This is a dermoscopic photograph of a skin lesion; a female patient about 35 years old.
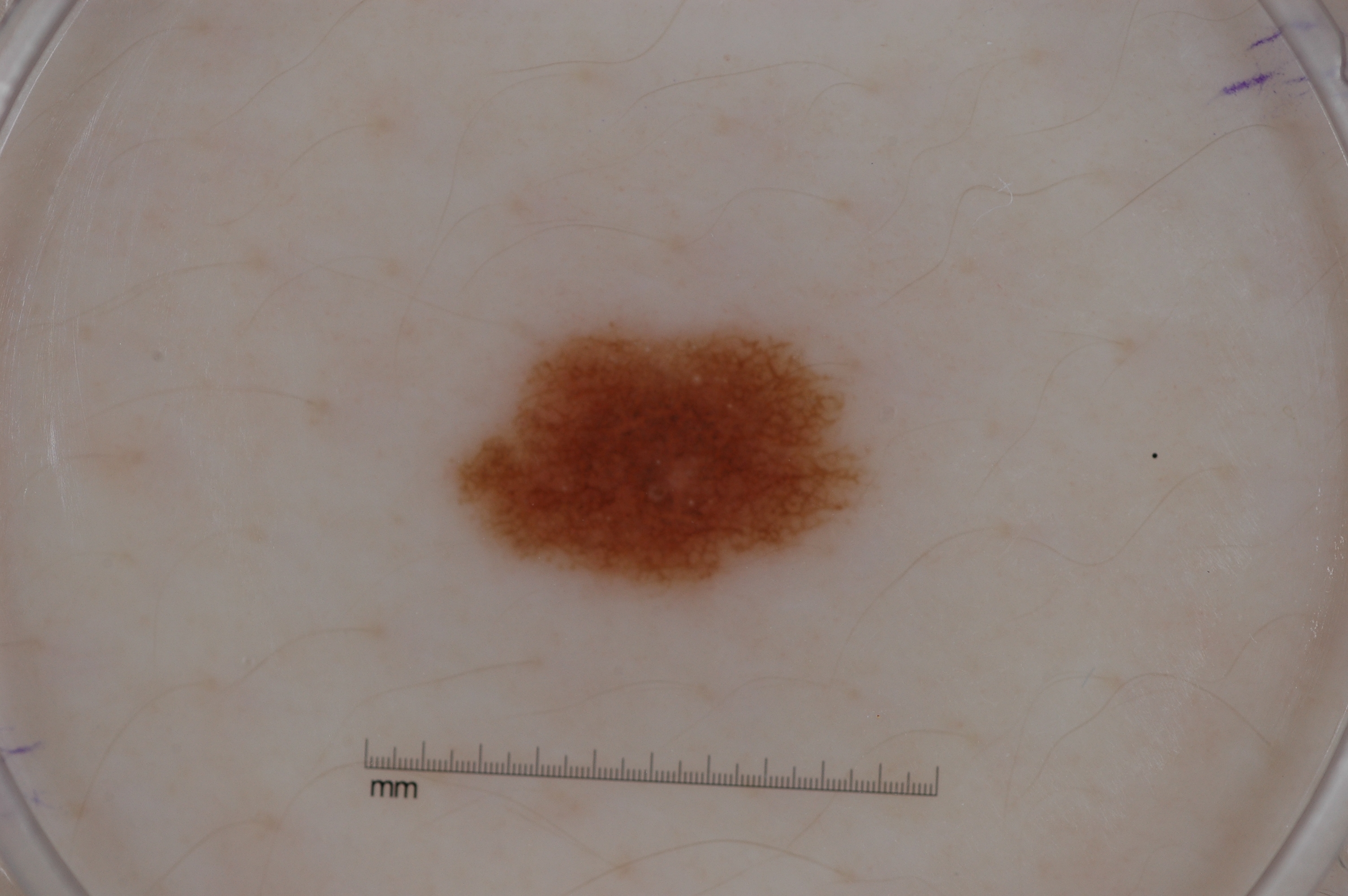The lesion takes up about 8% of the image. As (left, top, right, bottom), the visible lesion spans box(441, 313, 881, 610). Dermoscopically, the lesion shows pigment network. Expert review diagnosed this as a melanocytic nevus.